No relevant systemic symptoms, the lesion is associated with bothersome appearance and itching, self-categorized by the patient as a rash, the condition has been present for three to twelve months, the photograph was taken at a distance, the lesion is described as rough or flaky, the patient is female:
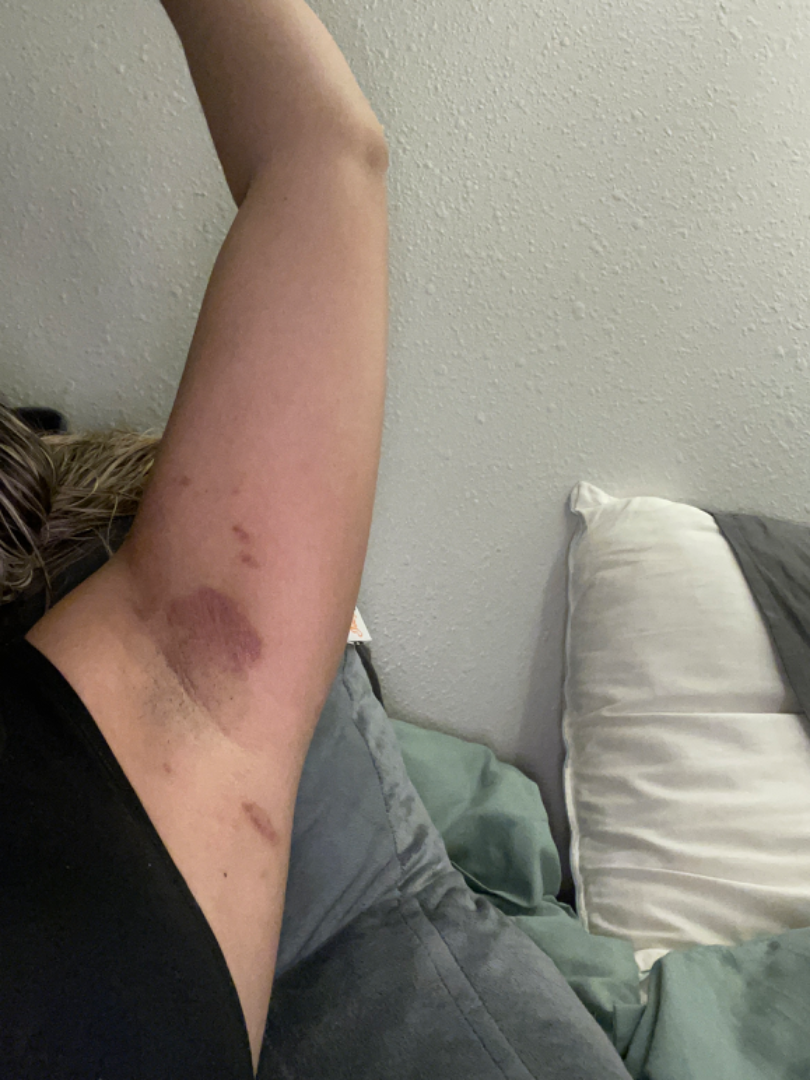Notes:
* clinical impression · Allergic Contact Dermatitis and Irritant Contact Dermatitis were each considered, in no particular order